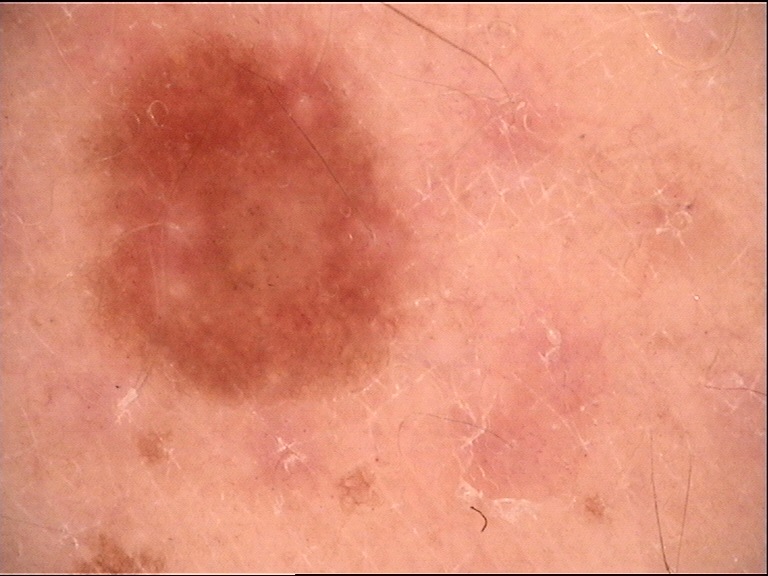Q: What kind of image is this?
A: dermoscopy
Q: What was the diagnostic impression?
A: dysplastic junctional nevus (expert consensus)